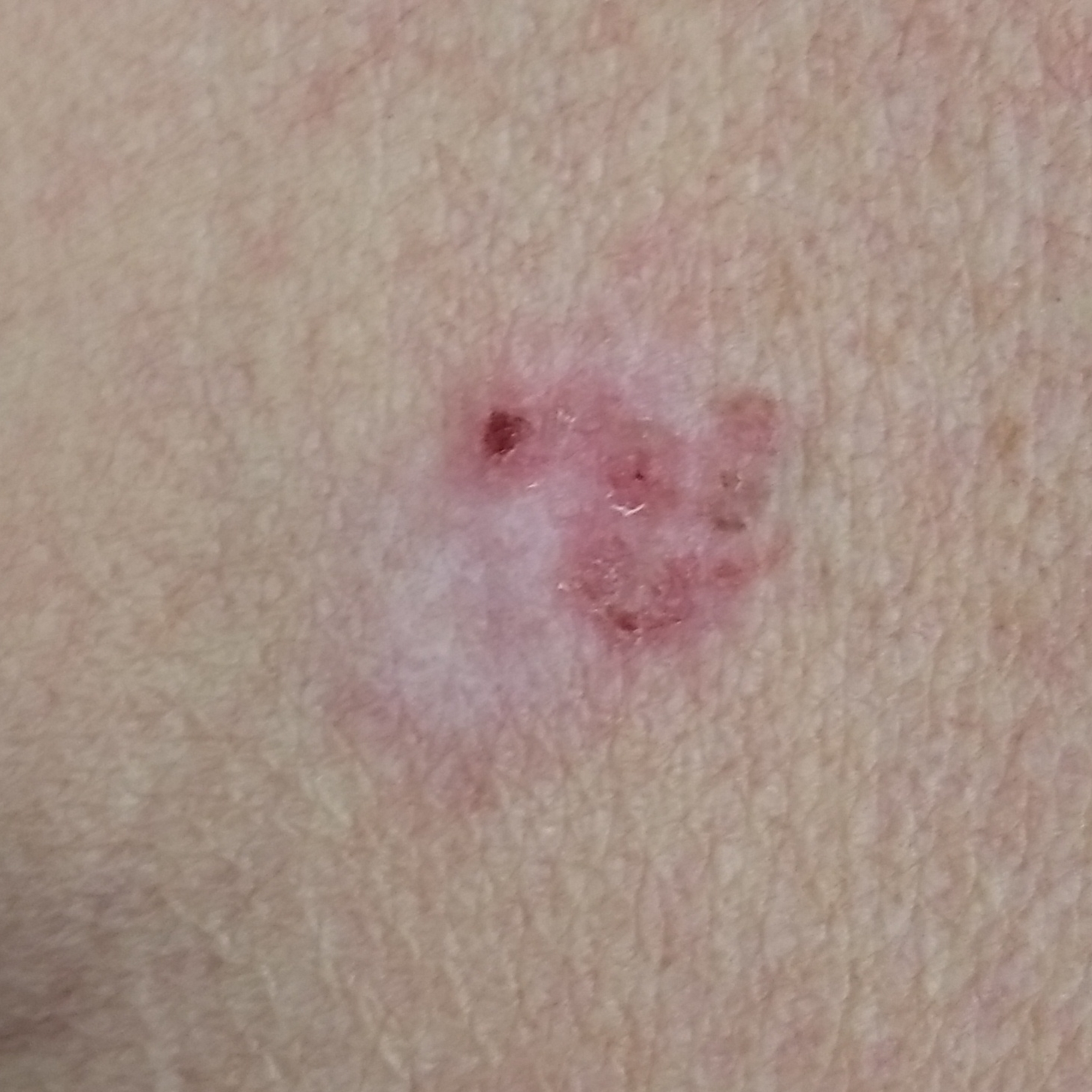Patient and lesion: A male subject 80 years of age. By history, prior malignancy (patient or family). A clinical photo of a skin lesion taken with a smartphone. The lesion is located on the chest. Measuring about 20 × 18 mm. Pathology: Biopsy-confirmed as a basal cell carcinoma.